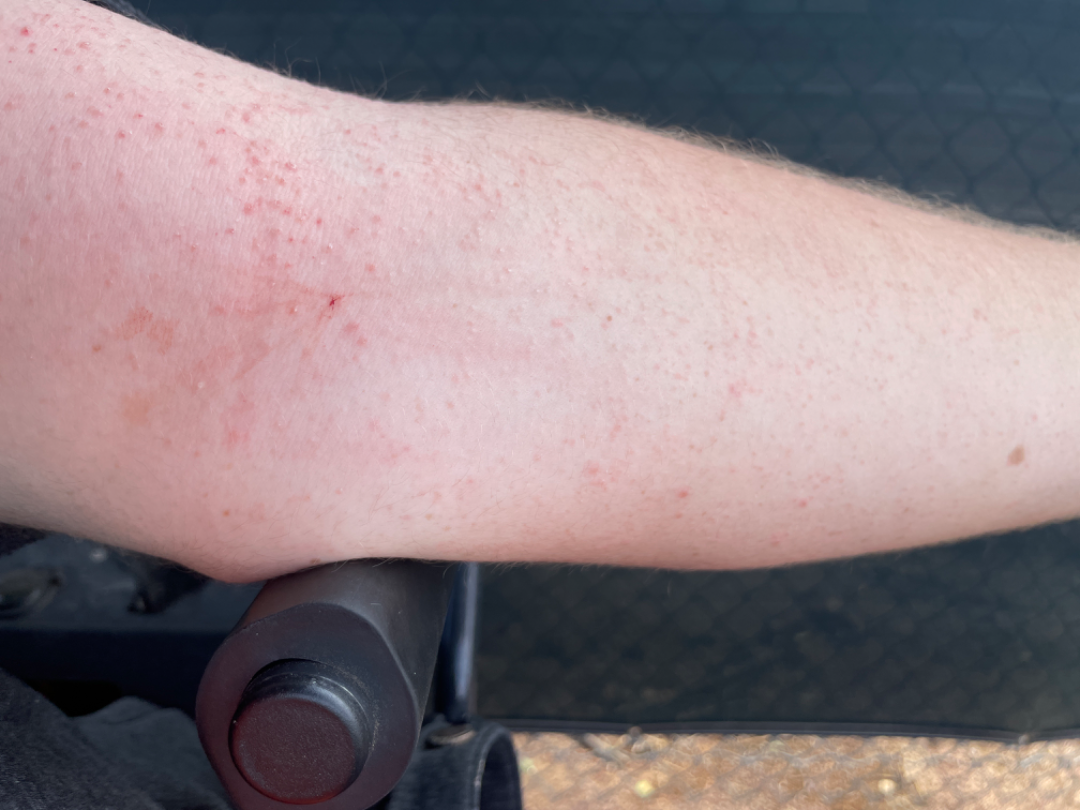Case summary:
* patient's own categorization · a rash
* body site · arm and head or neck
* texture · raised or bumpy
* view · at an angle
* assessment · Keratosis pilaris and Eczema were each considered, in no particular order; a more distant consideration is Folliculitis